FST II; lay reviewers estimated Monk Skin Tone 2 or 3 (two reviewer pools) · no associated systemic symptoms reported · the lesion is associated with enlargement · self-categorized by the patient as a rash · the lesion is described as raised or bumpy · close-up view · the contributor notes the condition has been present for less than one week.
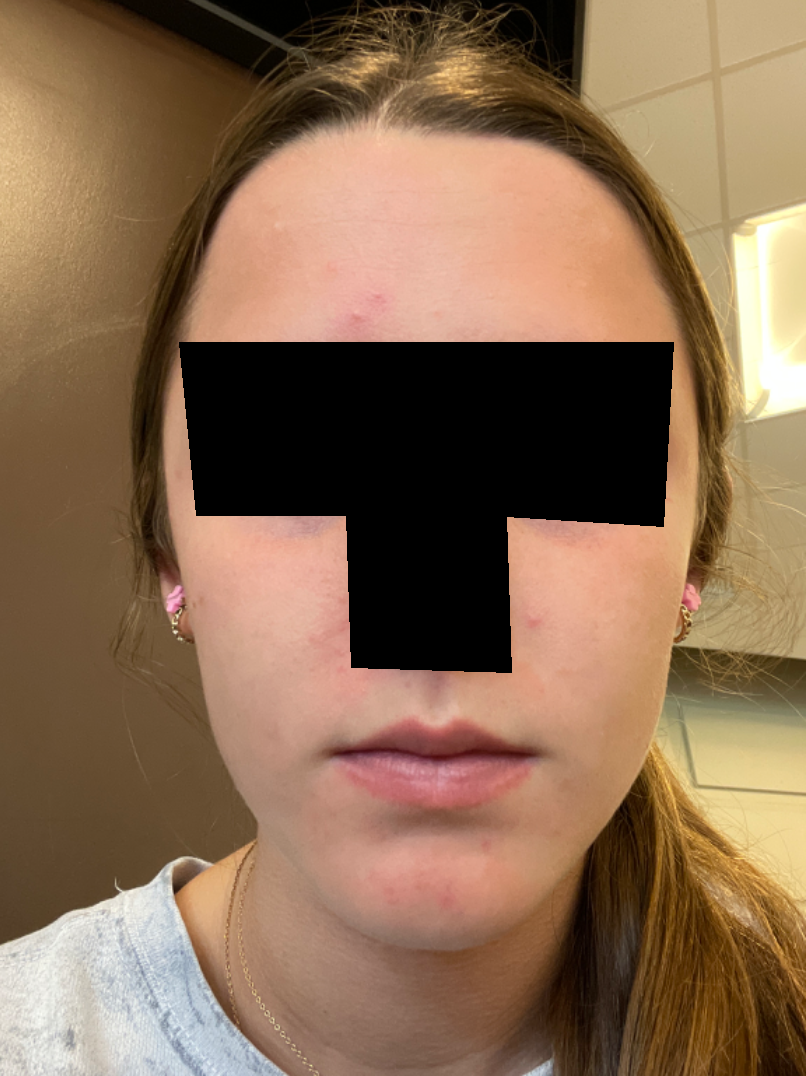Review: Most consistent with Acne.